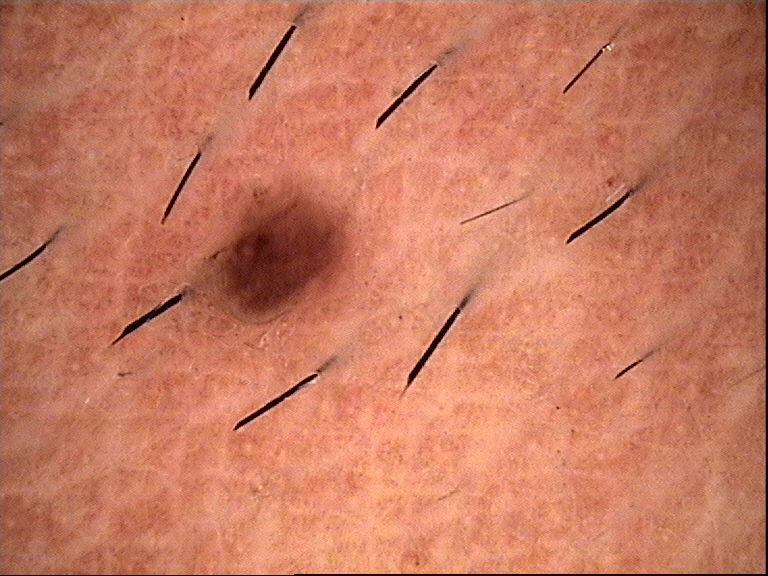A dermoscopic photograph of a skin lesion. Diagnosed as a compound nevus.